The photograph was taken at an angle; the lesion involves the arm; the patient reports the condition has been present for less than one week; the patient reports the lesion is rough or flaky; female contributor, age 40–49:
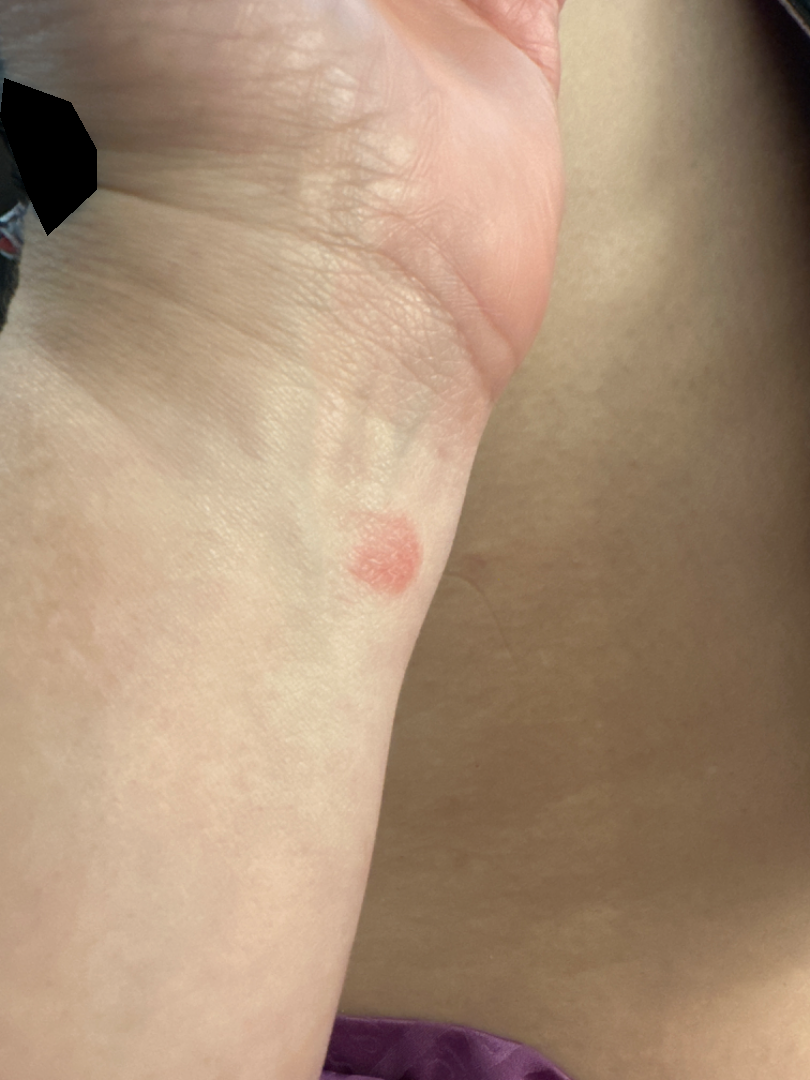Findings:
– assessment · the differential, in no particular order, includes Eczema and Allergic Contact Dermatitis